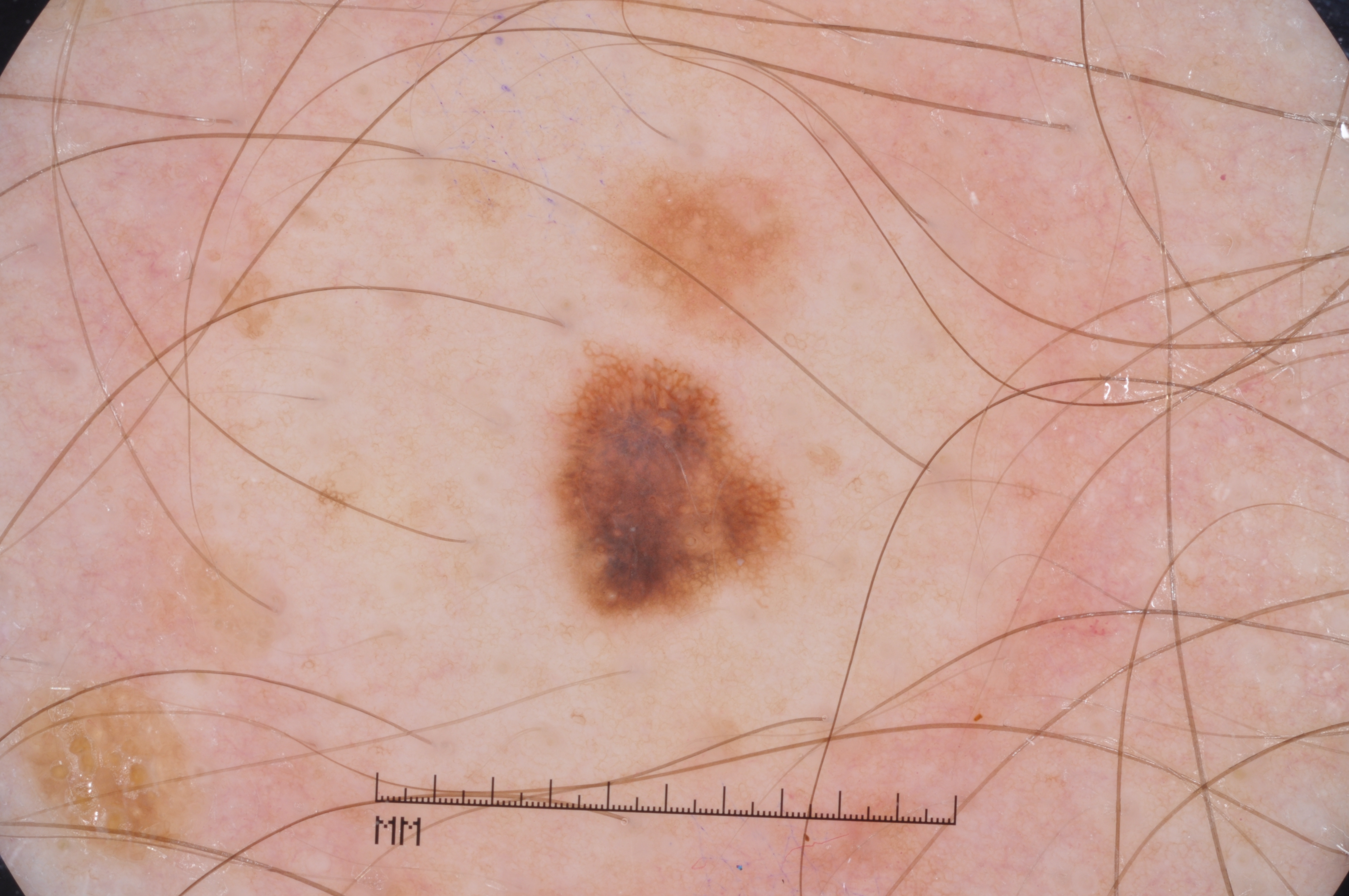subject = male, approximately 30 years of age | imaging = dermatoscopic image of a skin lesion | lesion location = [546,343,795,626] | dermoscopic findings = pigment network and milia-like cysts; absent: streaks and negative network | impression = a melanocytic nevus, a benign skin lesion.